A dermoscopy image of a single skin lesion.
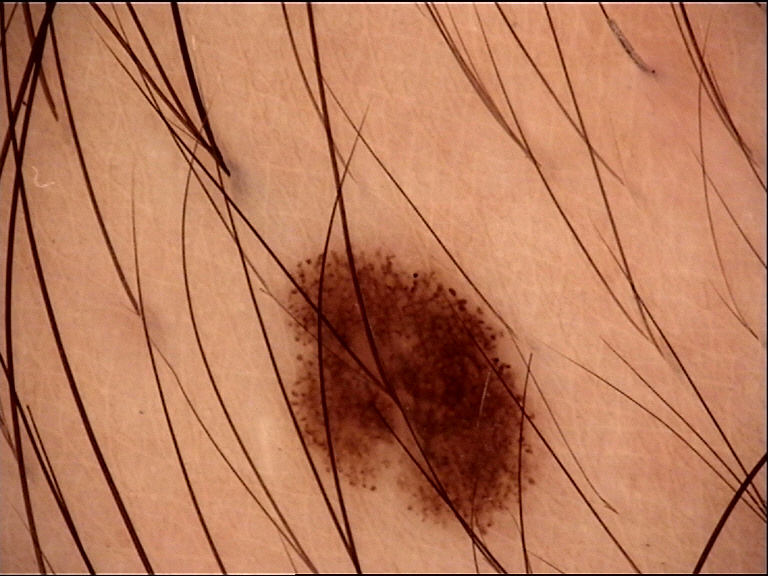category: banal; assessment: junctional nevus (expert consensus).